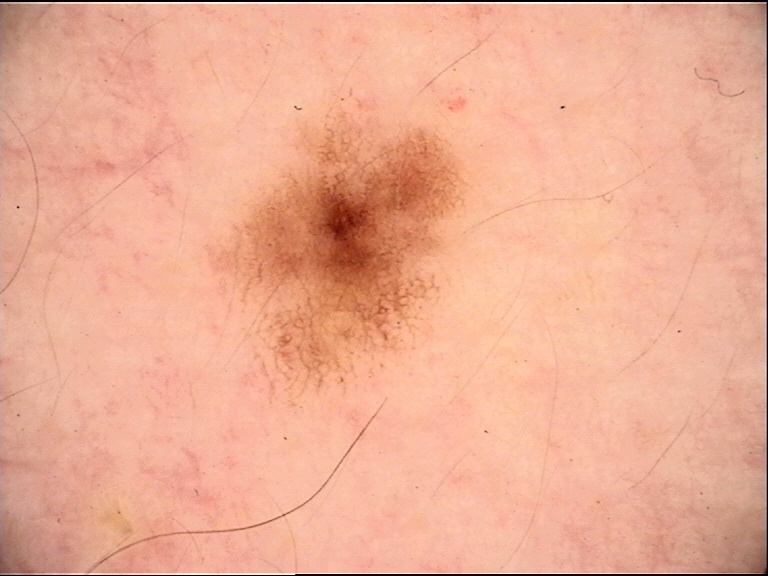The diagnosis was a dysplastic junctional nevus.